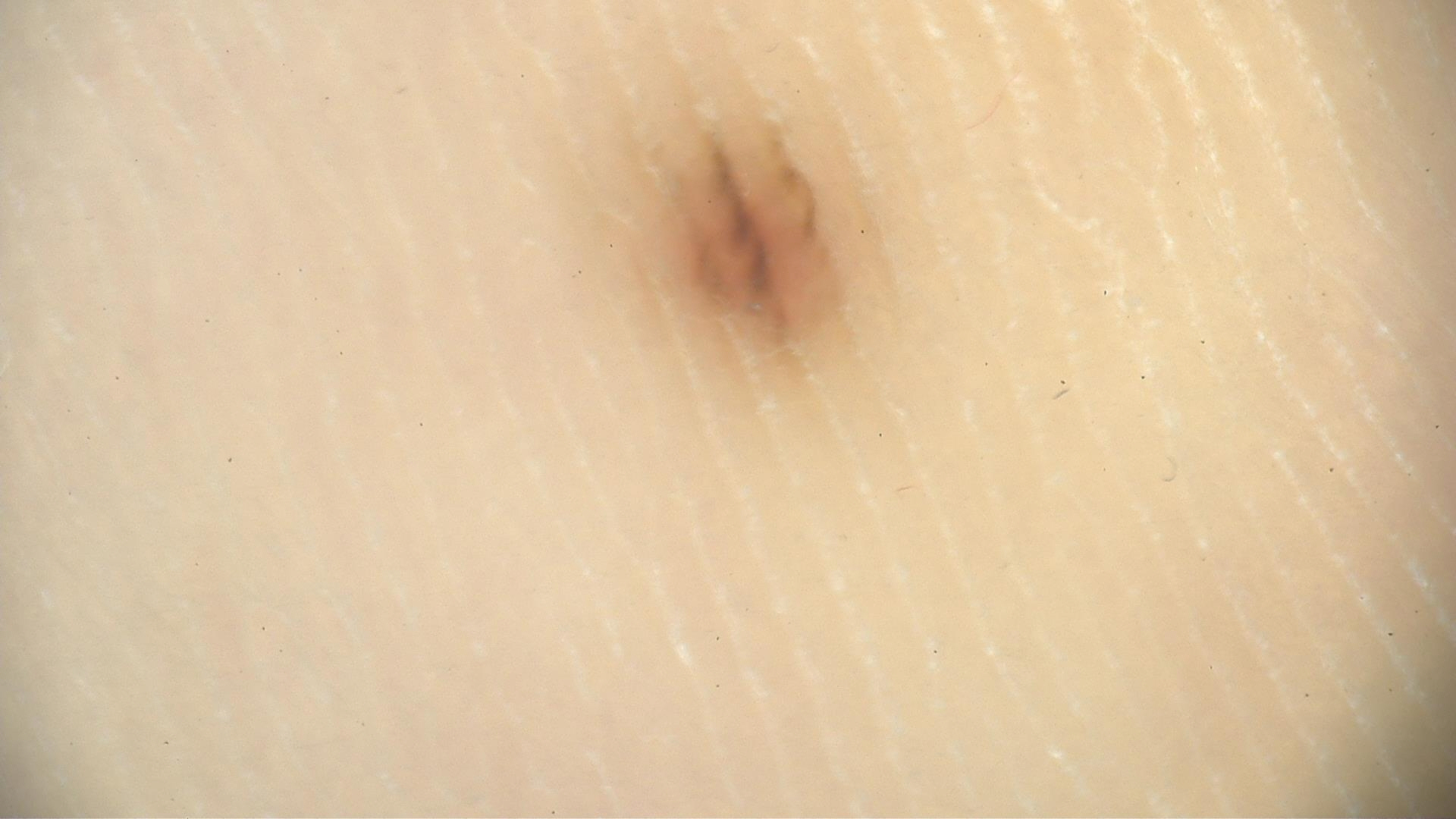diagnostic label=acral dysplastic junctional nevus (expert consensus)